A dermatoscopic image of a skin lesion: 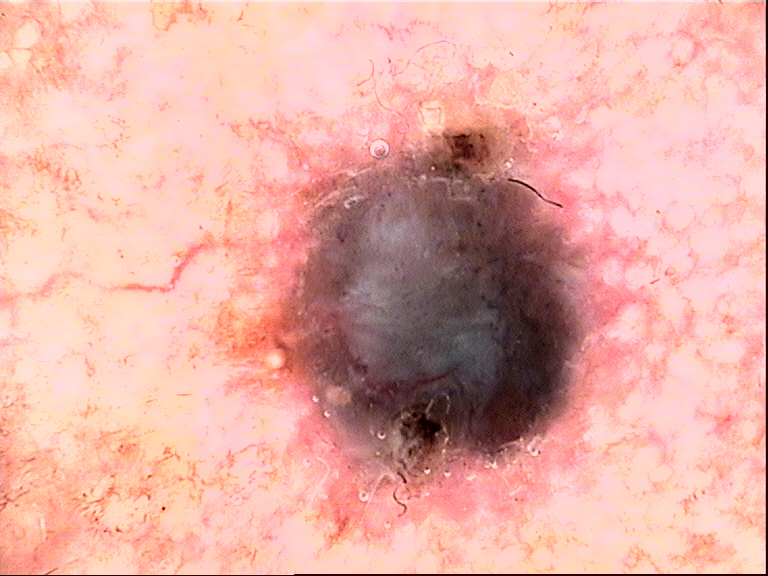{
  "lesion_type": {
    "main_class": "keratinocytic"
  },
  "diagnosis": {
    "name": "basal cell carcinoma",
    "code": "bcc",
    "malignancy": "malignant",
    "super_class": "non-melanocytic",
    "confirmation": "histopathology"
  }
}